The subject is a female aged 18–29, this image was taken at an angle, the back of the hand is involved:
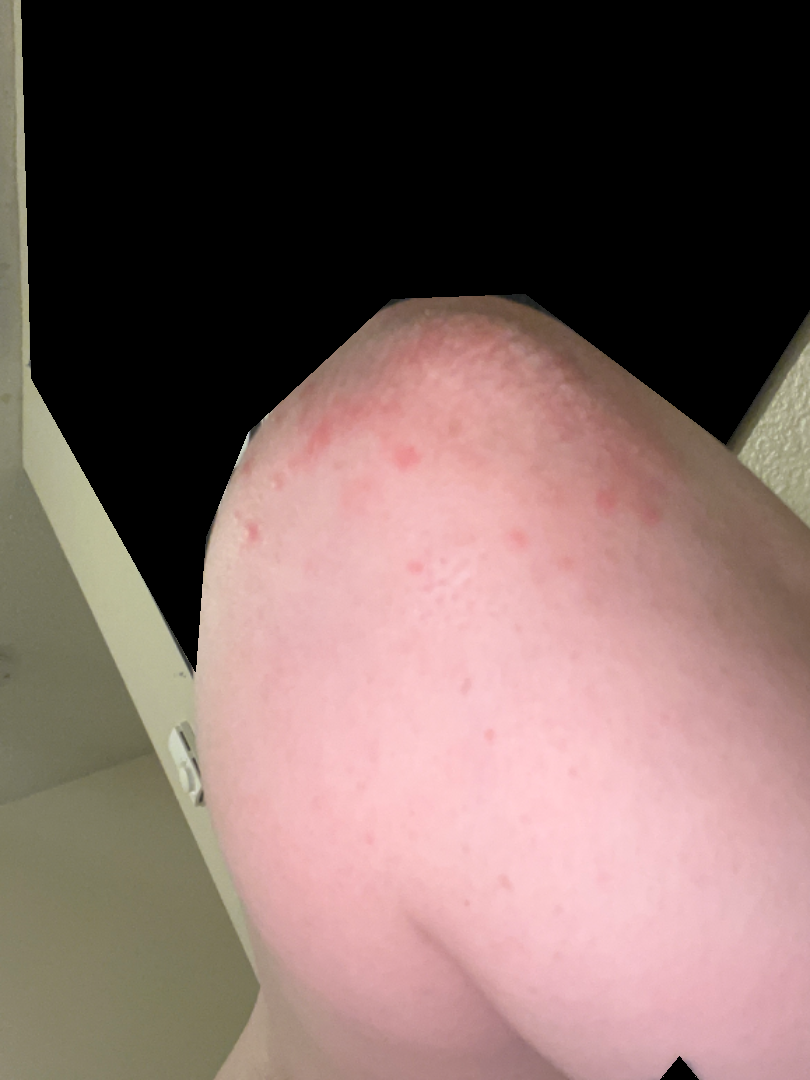lesion texture = rough or flaky
patient describes the issue as = a rash
present for = less than one week
lesion symptoms = itching
impression = three independent reviewers: favoring Psoriasis; less likely is Dermatitis herpetiformis; a remote consideration is Allergic Contact Dermatitis; lower on the differential is Acute dermatitis, NOS; less probable is Eczema